The patient was assessed as FST II; the chart notes pesticide exposure; a male subject 41 years old; a clinical photograph of a skin lesion — 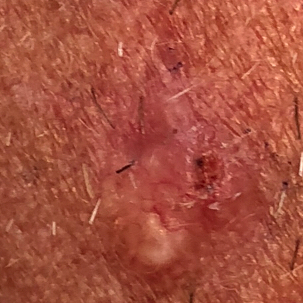site: the face; size: approx. 9 × 5 mm; reported symptoms: pain, elevation, itching, bleeding; diagnosis: basal cell carcinoma (biopsy-proven).